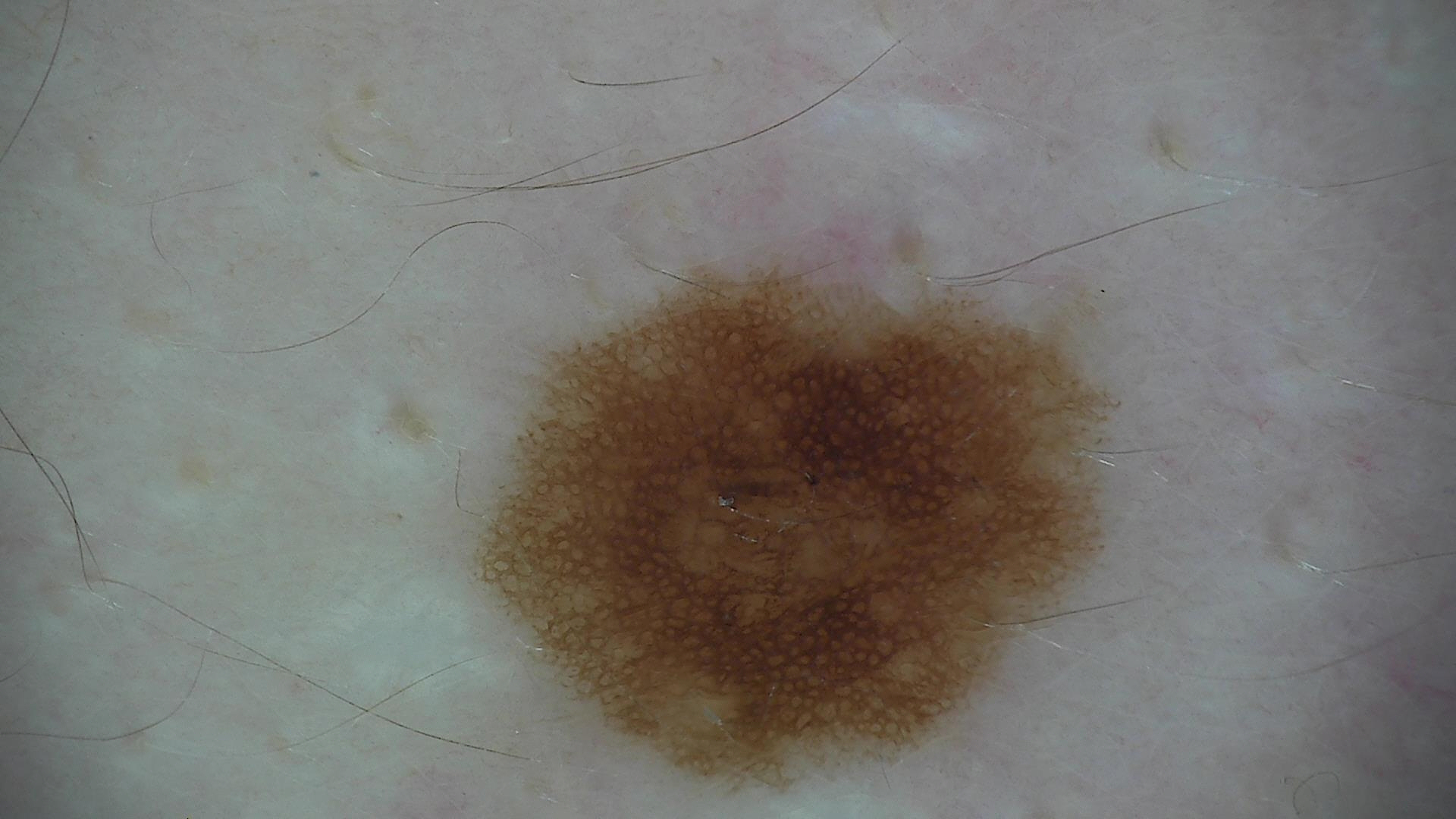Case:
A dermatoscopic image of a skin lesion.
Conclusion:
The diagnostic label was a dysplastic junctional nevus.